Recorded as skin type III. History notes prior skin cancer (patient or family) and pesticide exposure. A female patient 47 years of age. A clinical photo of a skin lesion taken with a smartphone:
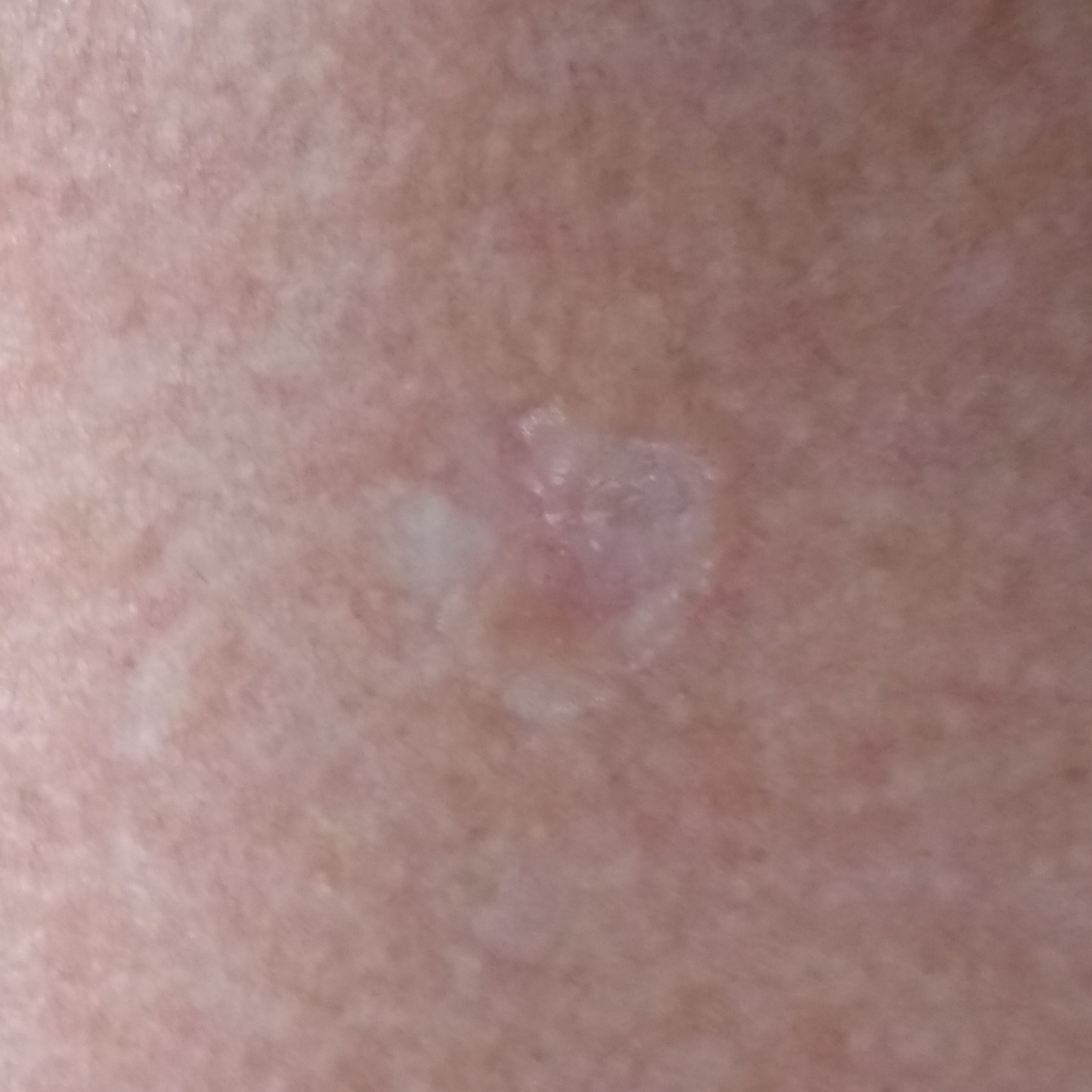site — the chest
lesion diameter — 11 × 11 mm
reported symptoms — pain, growth, itching, elevation, bleeding
diagnosis — basal cell carcinoma (biopsy-proven)